Dermoscopy of a skin lesion.
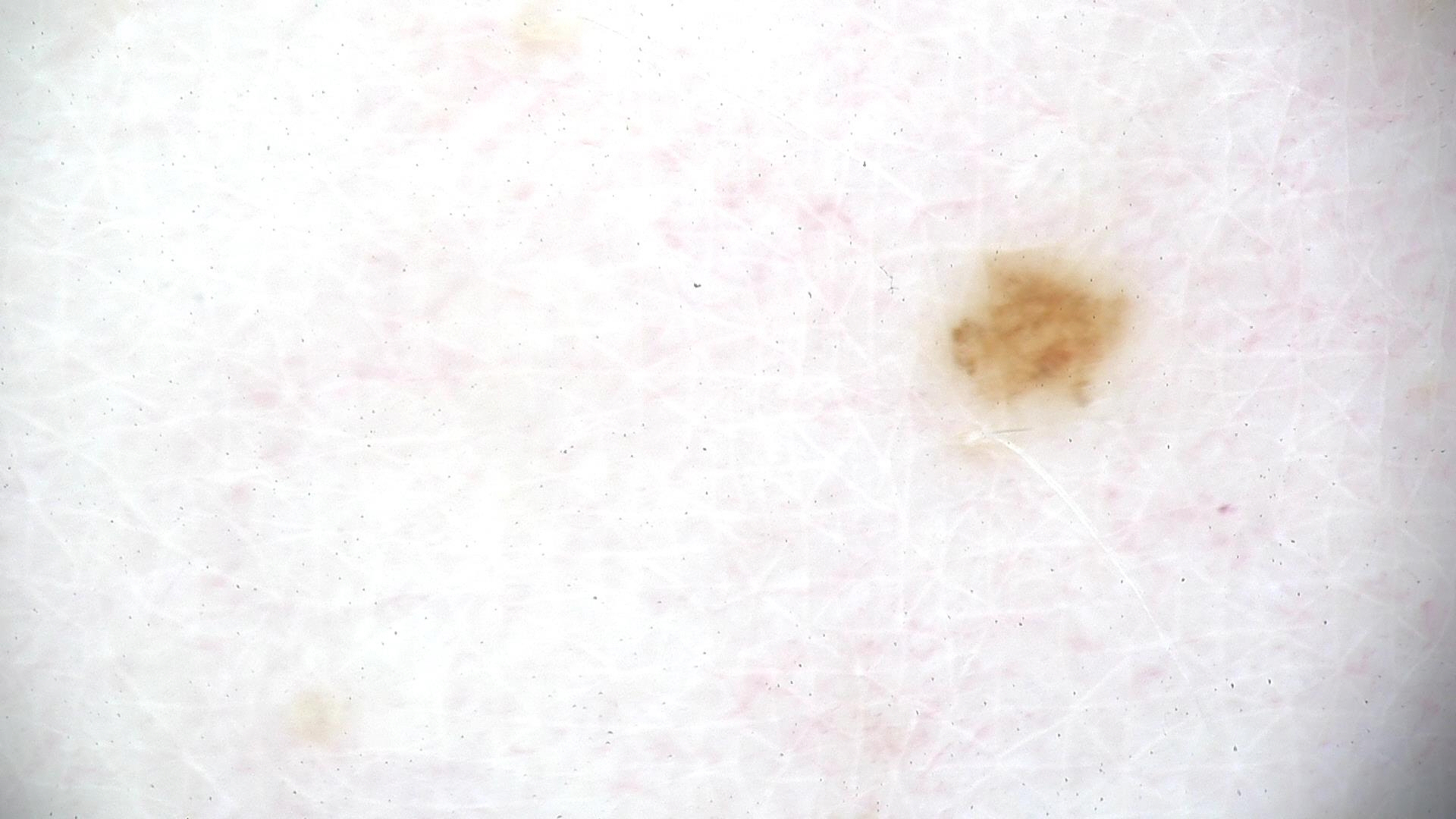Q: What is the diagnosis?
A: dysplastic junctional nevus (expert consensus)